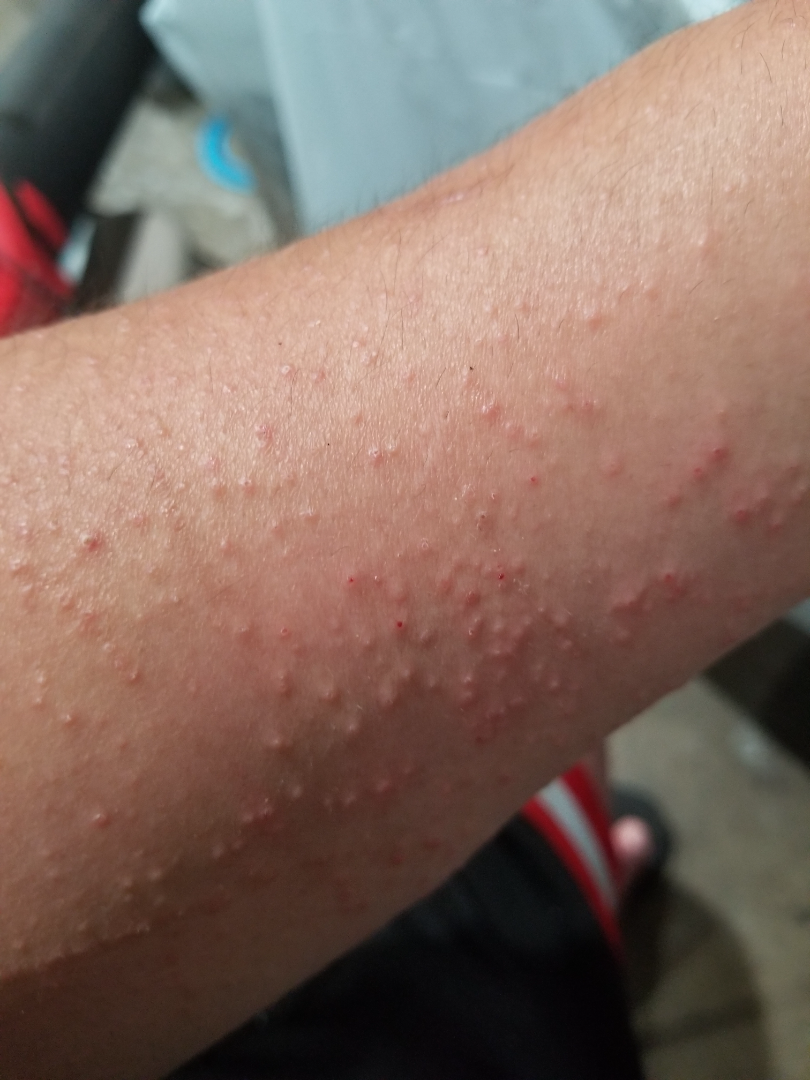<case>
  <shot_type>close-up</shot_type>
  <differential>
    <leading>Allergic Contact Dermatitis</leading>
    <considered>Insect Bite, Eczema</considered>
  </differential>
</case>